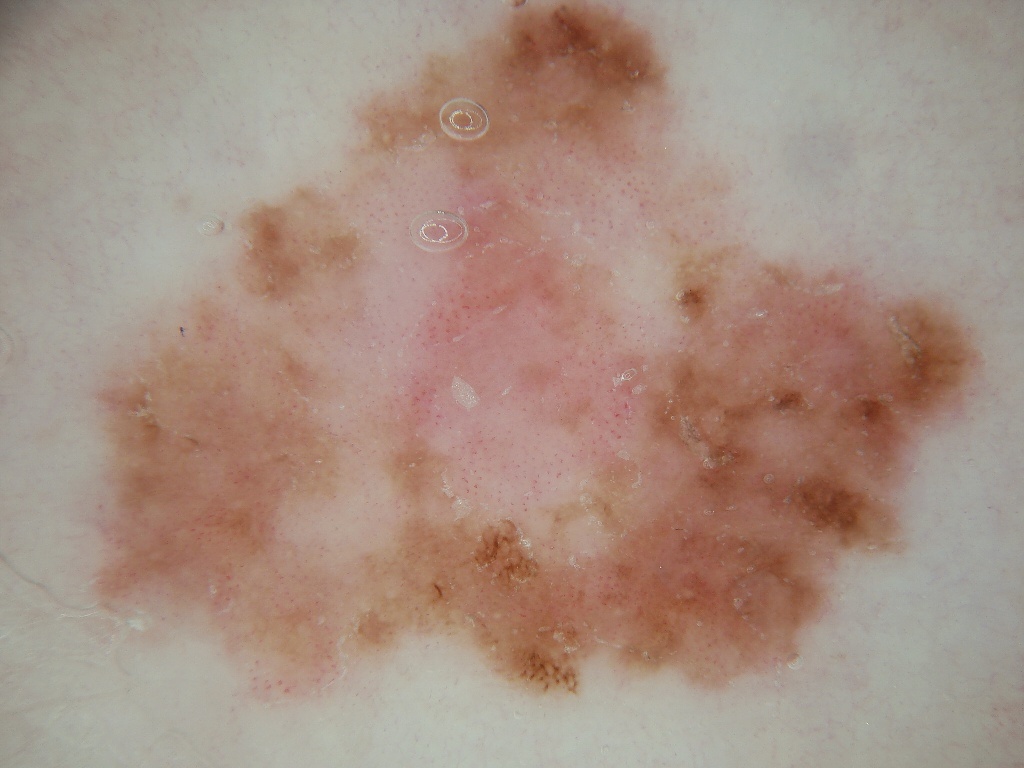A dermoscopic image of a skin lesion. The lesion spans left=63, top=0, right=987, bottom=698. On dermoscopy, the lesion shows pigment network. Histopathological examination showed a melanoma, a malignant skin lesion.